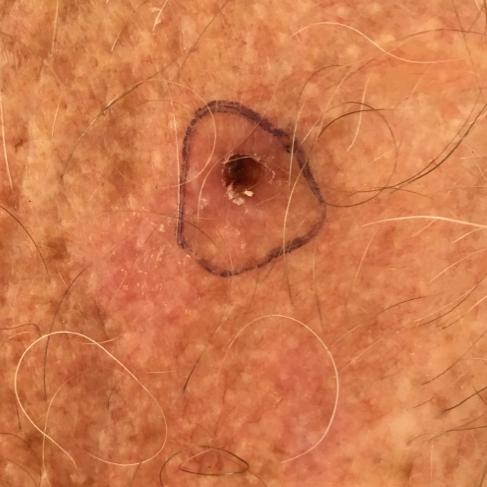Q: What is the patient's skin type?
A: III
Q: How was this image acquired?
A: smartphone clinical photo
Q: Tell me about the patient.
A: male, 69 years of age
Q: Where on the body is the lesion?
A: the back
Q: Lesion size?
A: approx. 4 × 4 mm
Q: What is this lesion?
A: basal cell carcinoma (biopsy-proven)